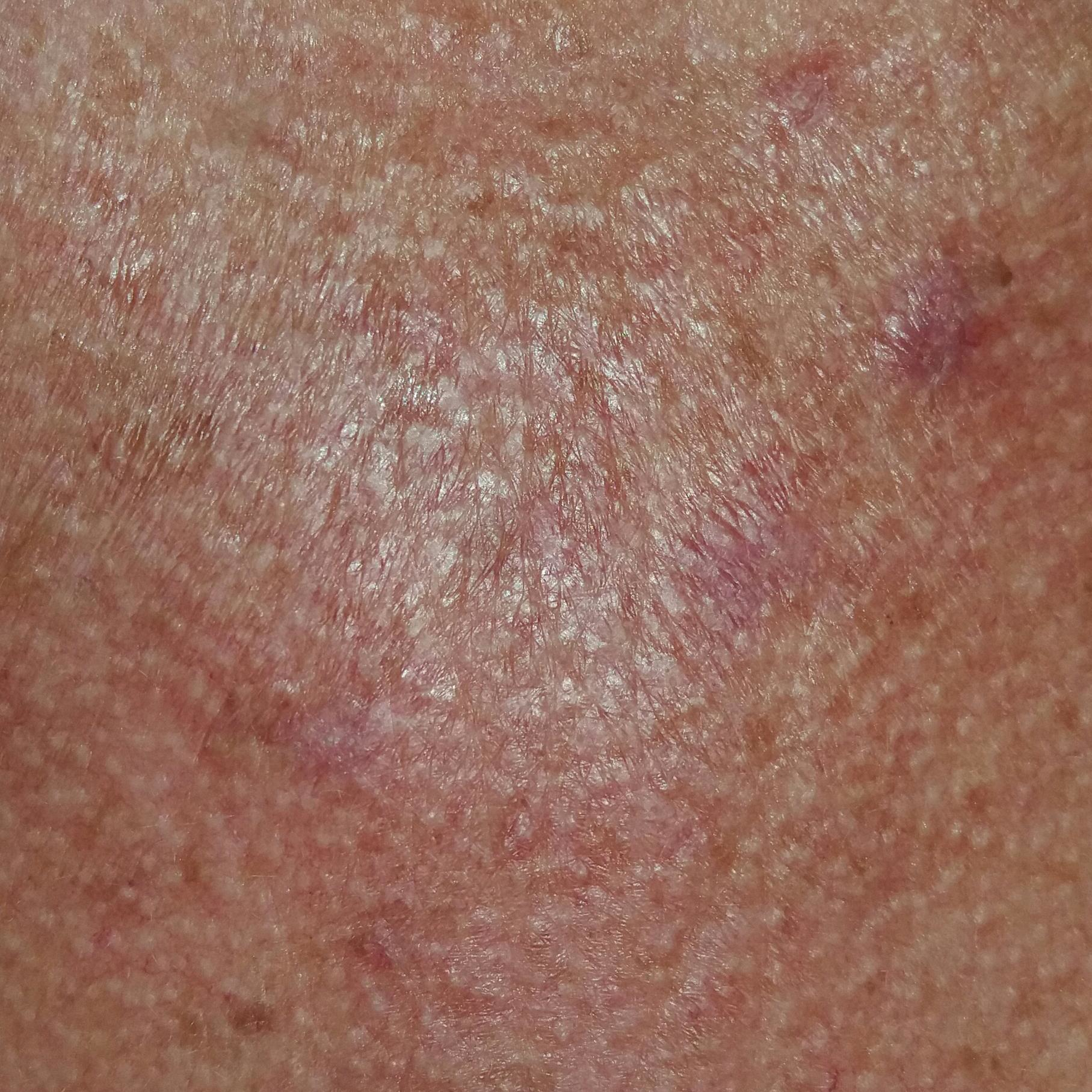image: smartphone clinical photo | risk factors: prior malignancy (patient or family), prior skin cancer (patient or family), no alcohol use | patient: female, 55 years old | Fitzpatrick: II | location: the chest | lesion size: 6x5 mm | symptoms: itching | diagnosis: actinic keratosis (clinical consensus).